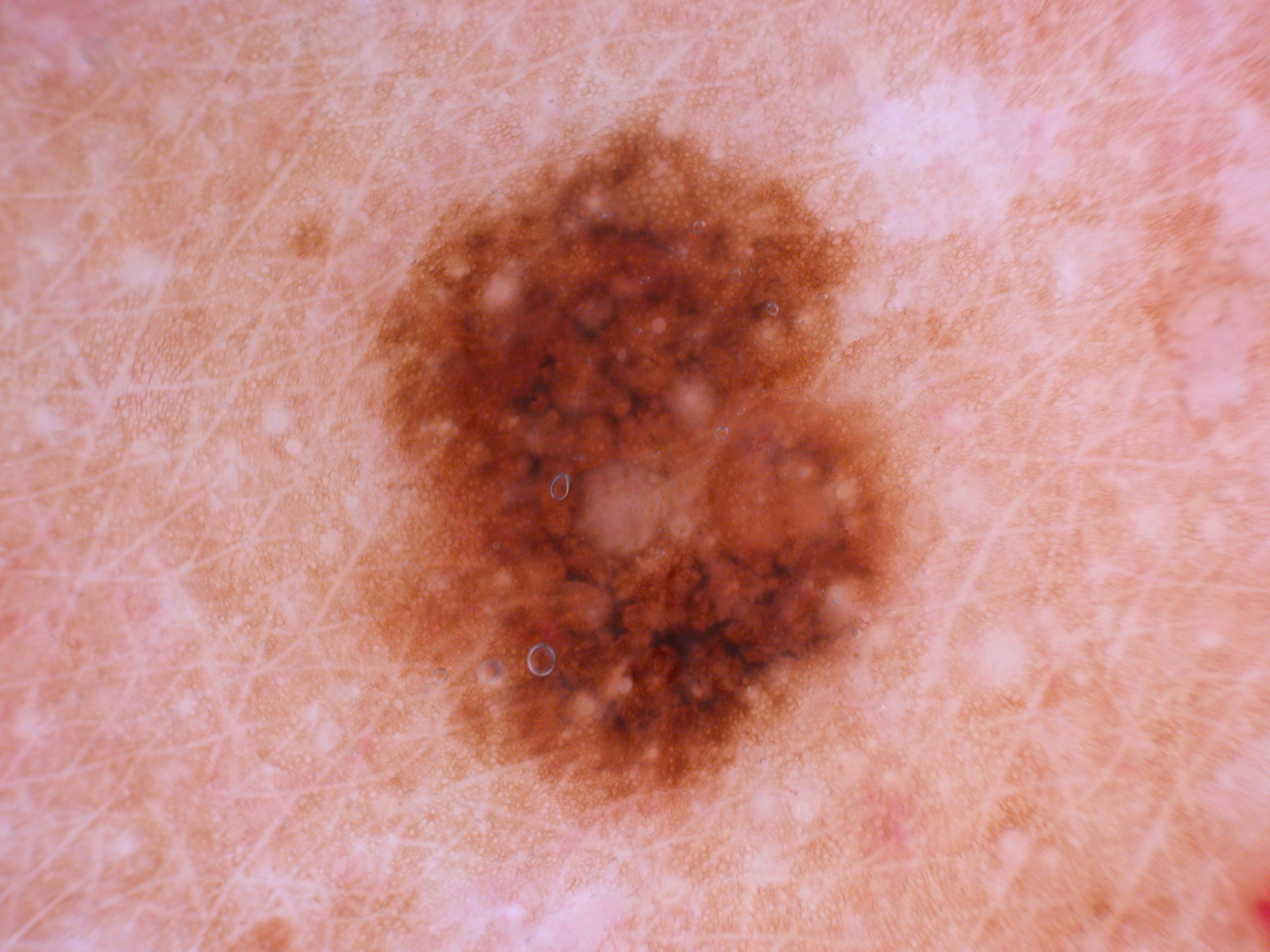Findings:
A dermatoscopic image of a skin lesion. Dermoscopically, the lesion shows pigment network; no milia-like cysts, streaks, negative network, or globules. In (x1, y1, x2, y2) order, the lesion is bounded by 331/110/920/825. The lesion covers approximately 24% of the dermoscopic field.
Conclusion:
The lesion was assessed as a melanocytic nevus, a benign skin lesion.